The photo was captured at a distance · the contributor is 30–39, male.
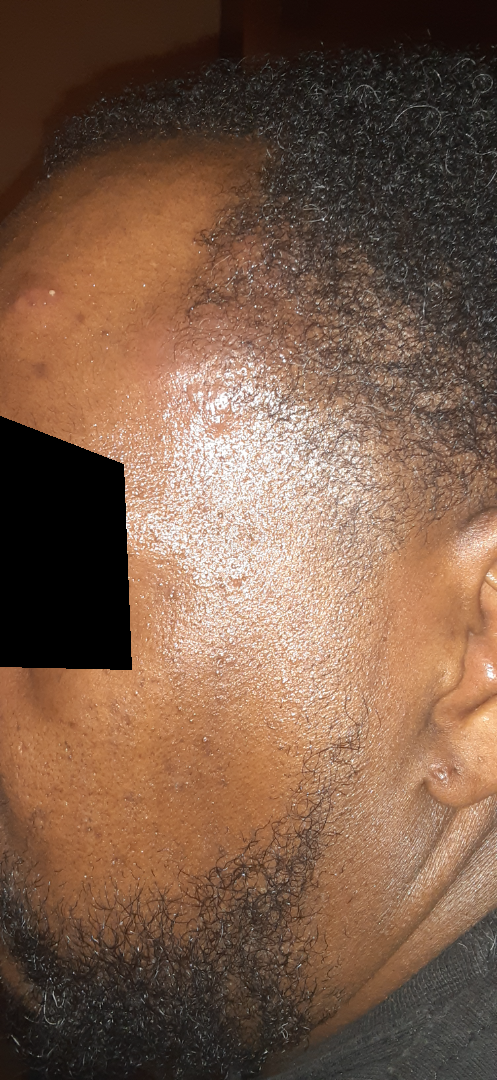| feature | finding |
|---|---|
| described texture | raised or bumpy |
| patient's own categorization | a rash |
| duration | less than one week |
| reported symptoms | pain |
| dermatologist impression | Pemphigus vulgaris (50%); Acne (50%) |